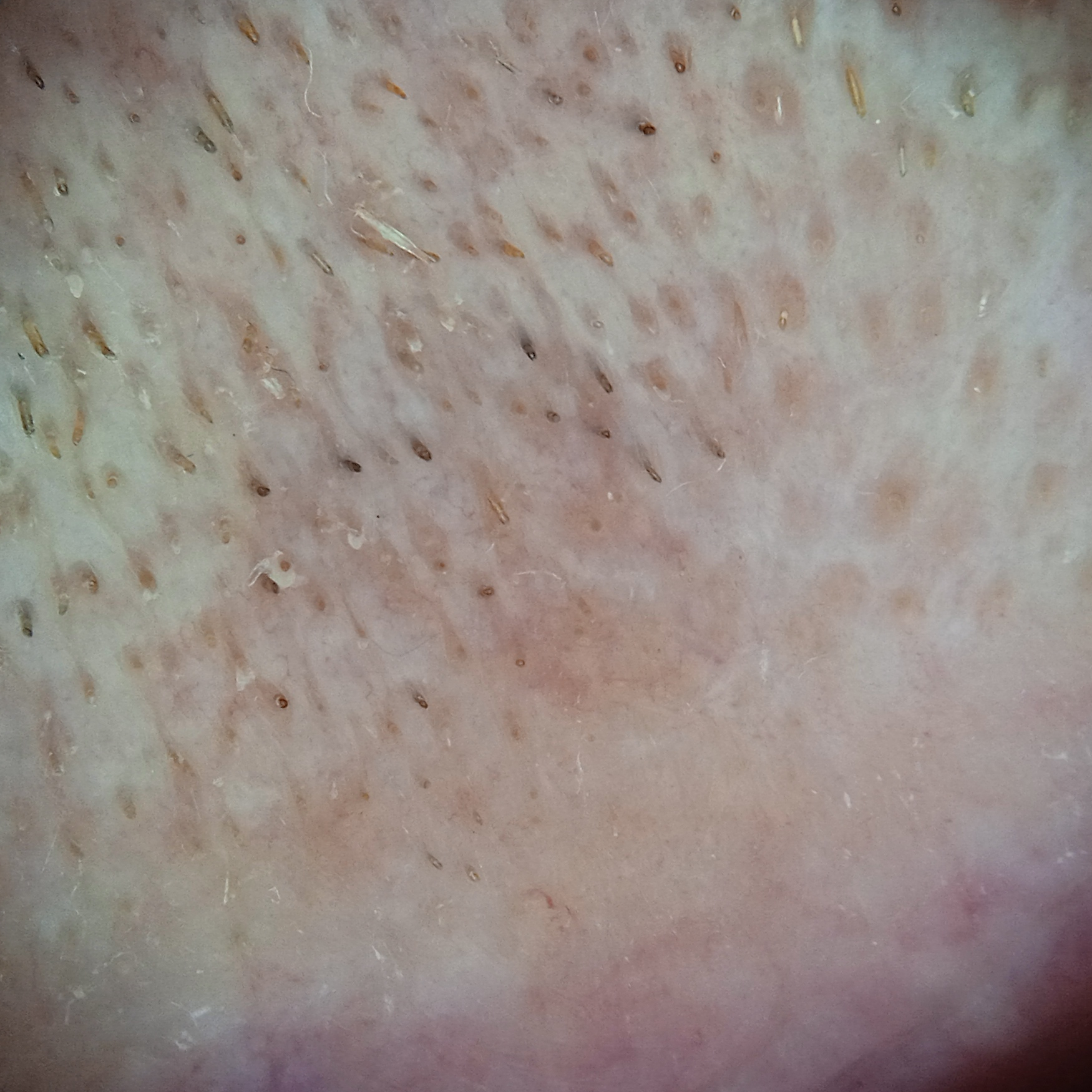Four dermatologists reviewed the lesion; the consensus was an actinic keratosis.